The patient says their skin reddens painfully with sun exposure; the patient describes having a moderate number of moles; on a questionnaire the patient reported no personal history of cancer and no sunbed use; a dermoscopic image of a skin lesion; imaged for a research study, with no referral diagnosis recorded; a female subject 81 years old: 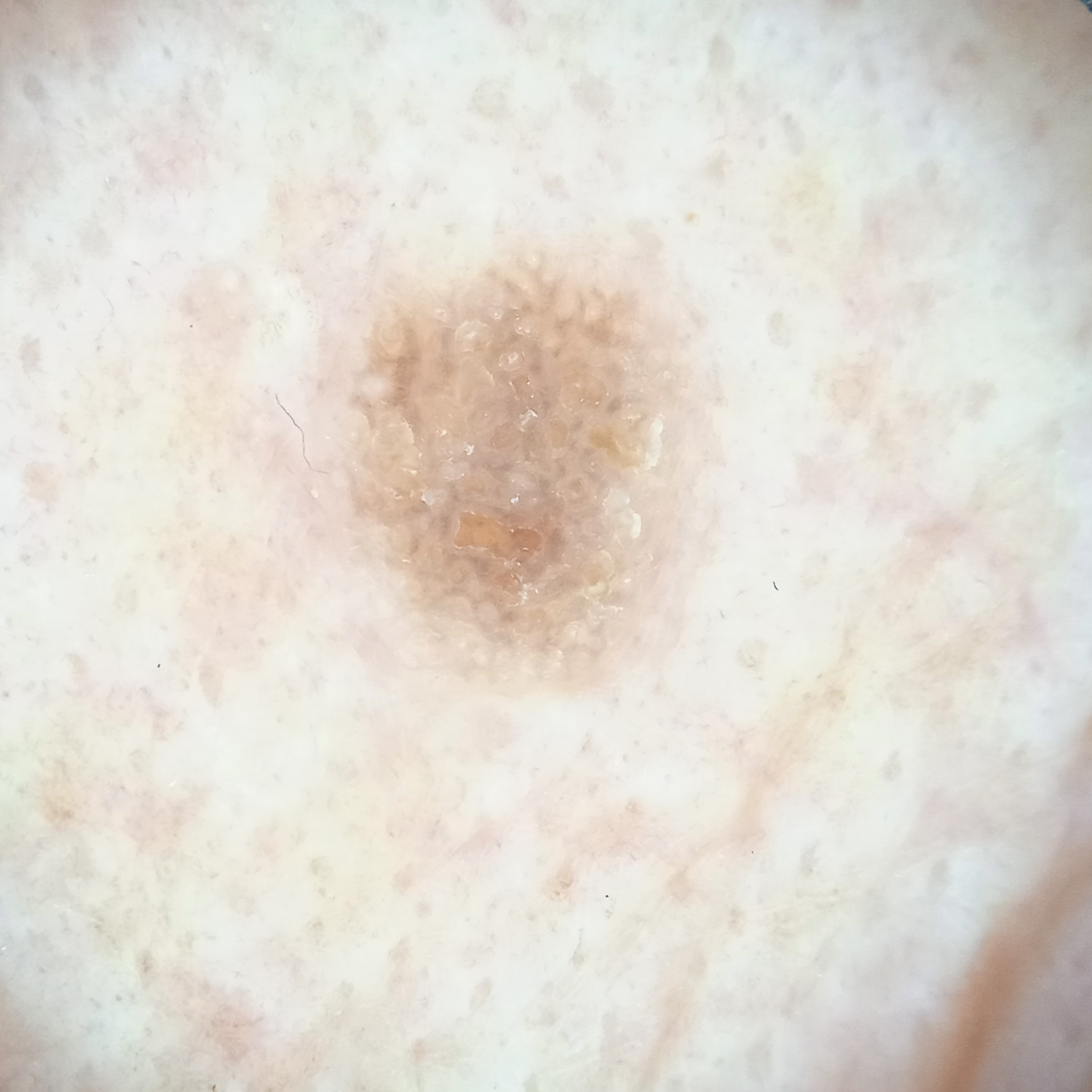Case summary:
The lesion is located on the face. Measuring roughly 5.3 mm.
Impression:
The lesion was assessed as a seborrheic keratosis.